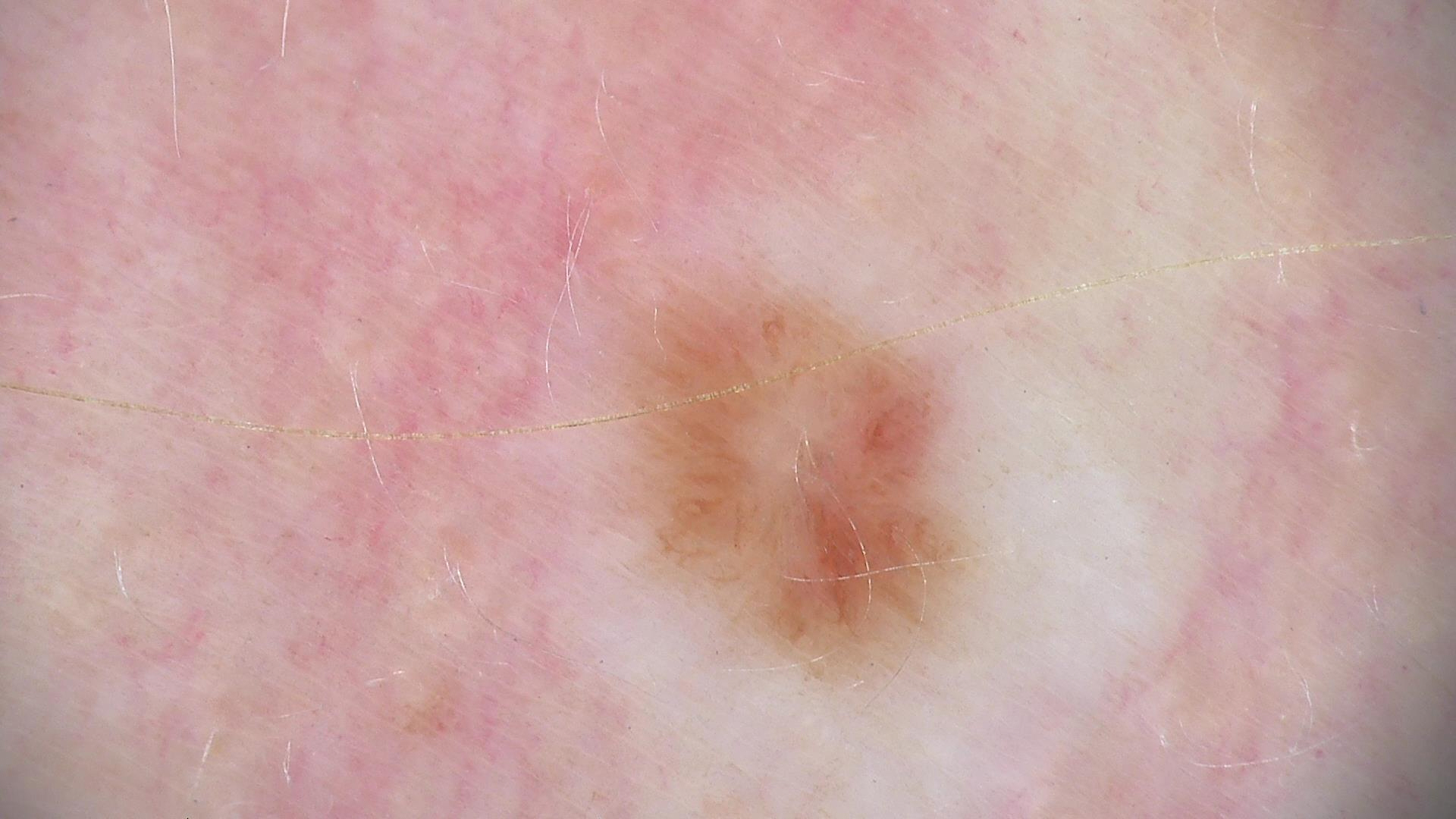The diagnosis was a dysplastic junctional nevus.